A dermatoscopic image of a skin lesion — 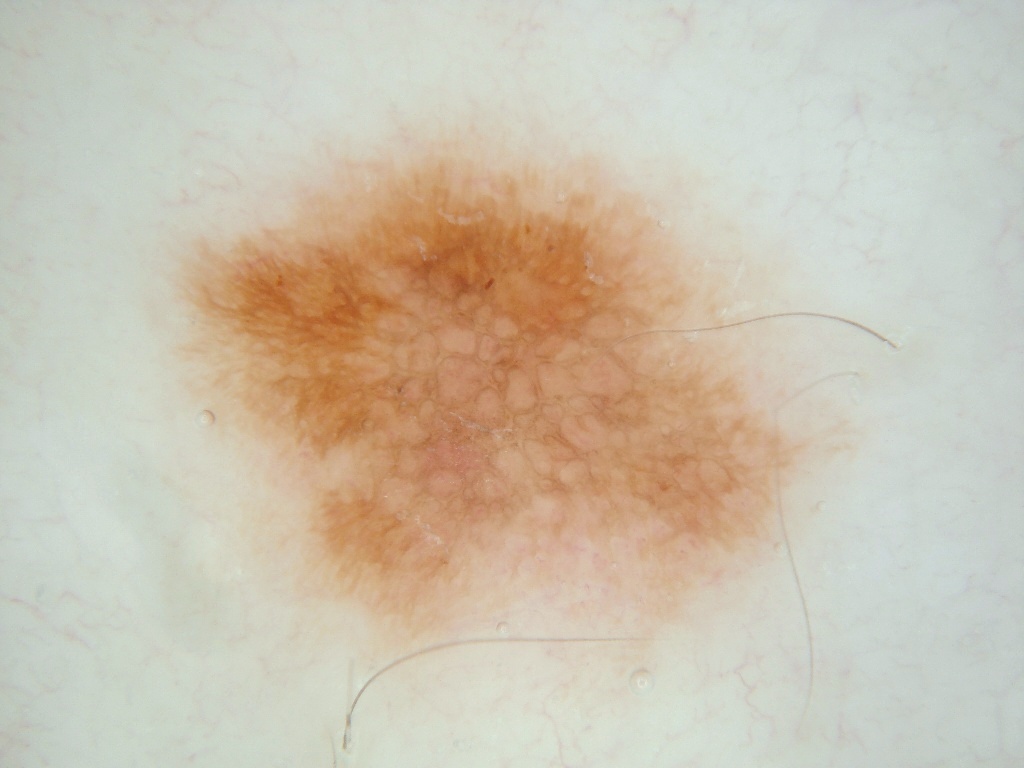The lesion's extent is x1=169 y1=129 x2=813 y2=657.
Dermoscopic examination shows streaks and pigment network.
Diagnosed as a melanocytic nevus.